Dermoscopy of a skin lesion.
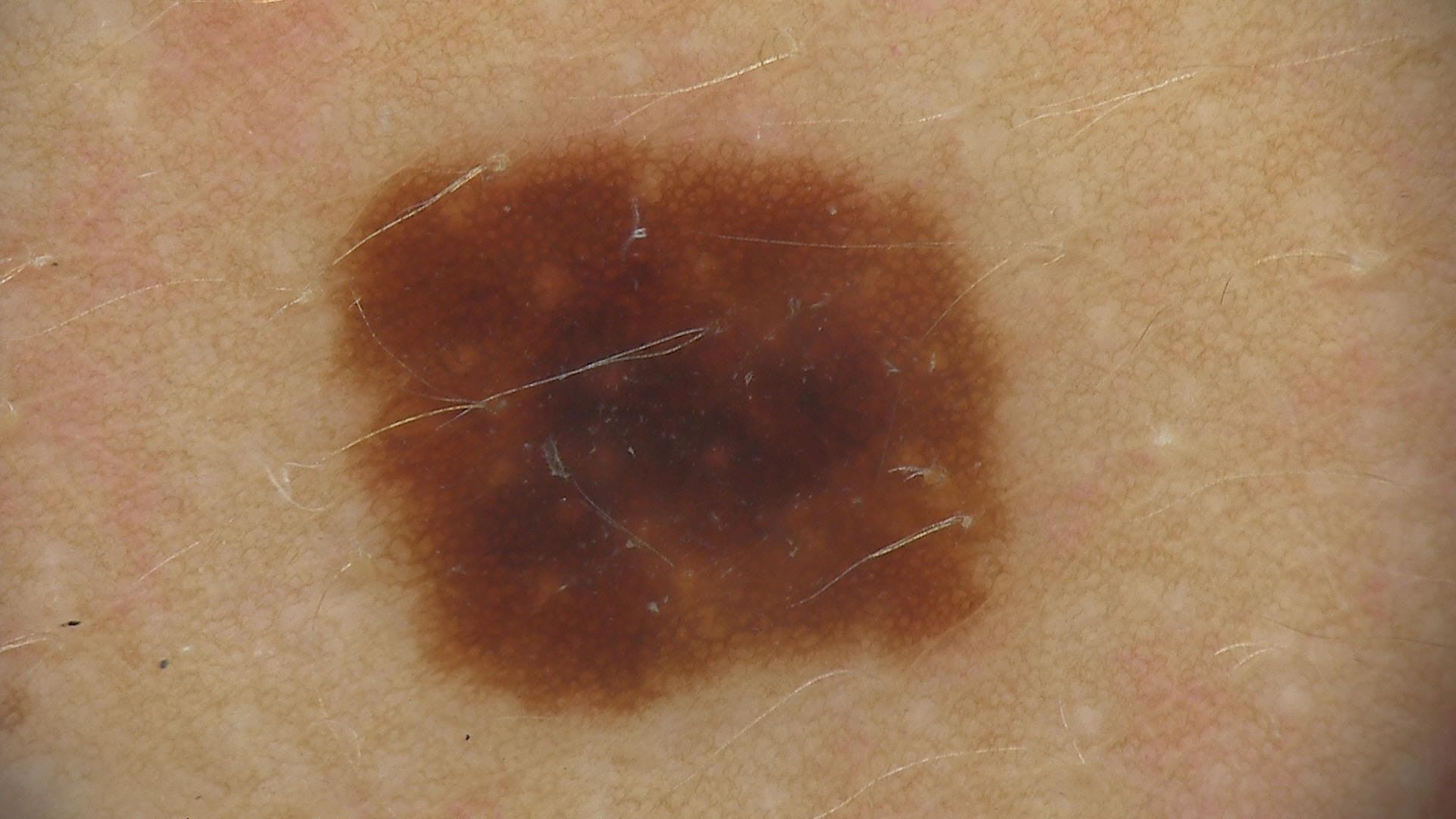Labeled as a dysplastic junctional nevus.